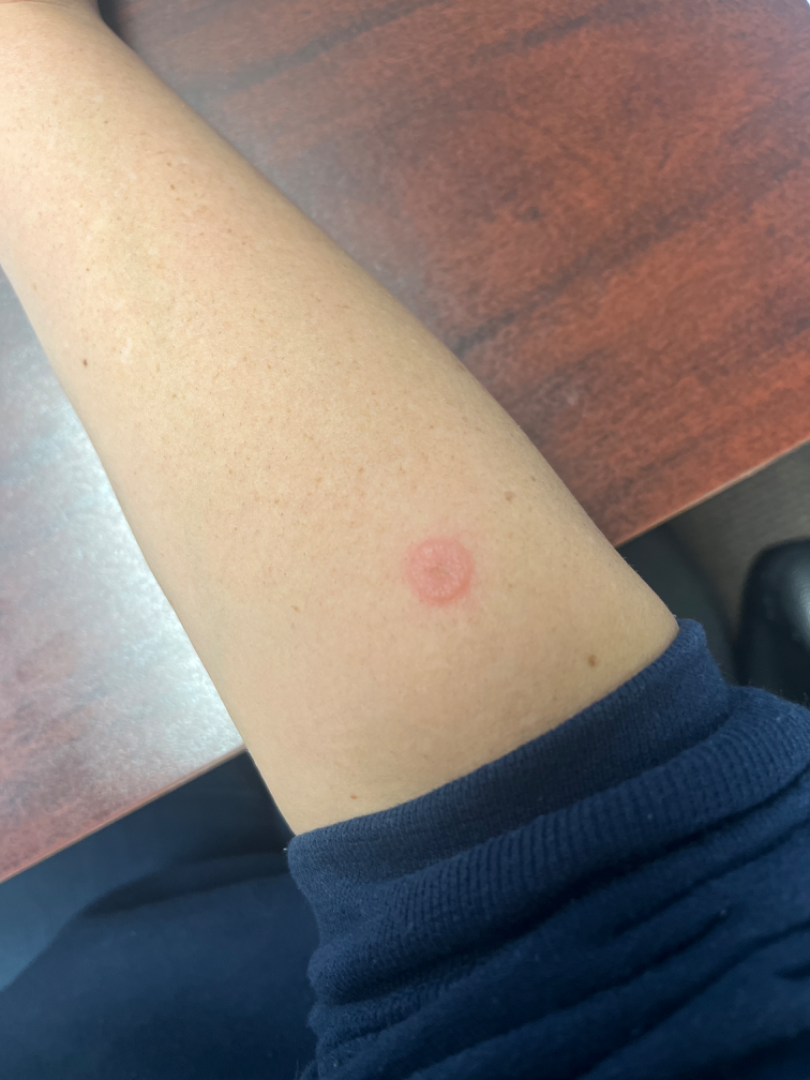Notes:
• assessment · indeterminate
• shot type · at a distance